A dermoscopic close-up of a skin lesion:
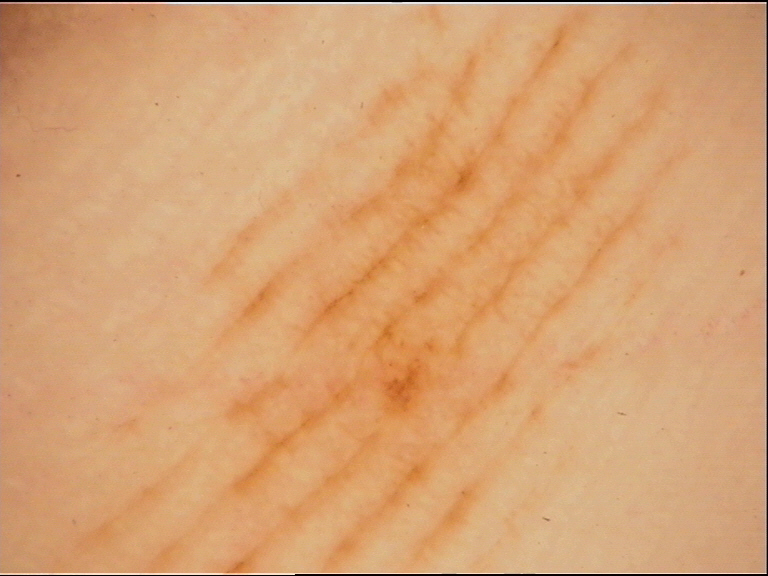The morphology is that of a banal lesion.
Consistent with an acral junctional nevus.